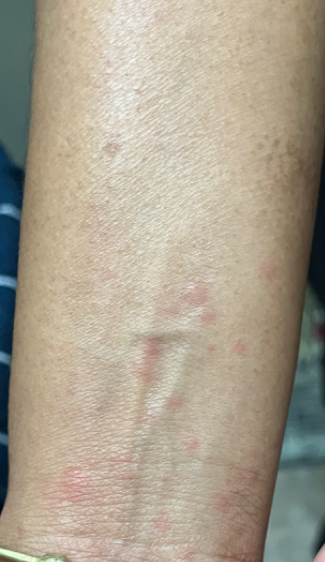{
  "shot_type": "close-up",
  "differential": {
    "leading": [
      "Lichen planus/lichenoid eruption"
    ],
    "considered": [
      "Insect Bite"
    ]
  }
}